A dermoscopic close-up of a skin lesion.
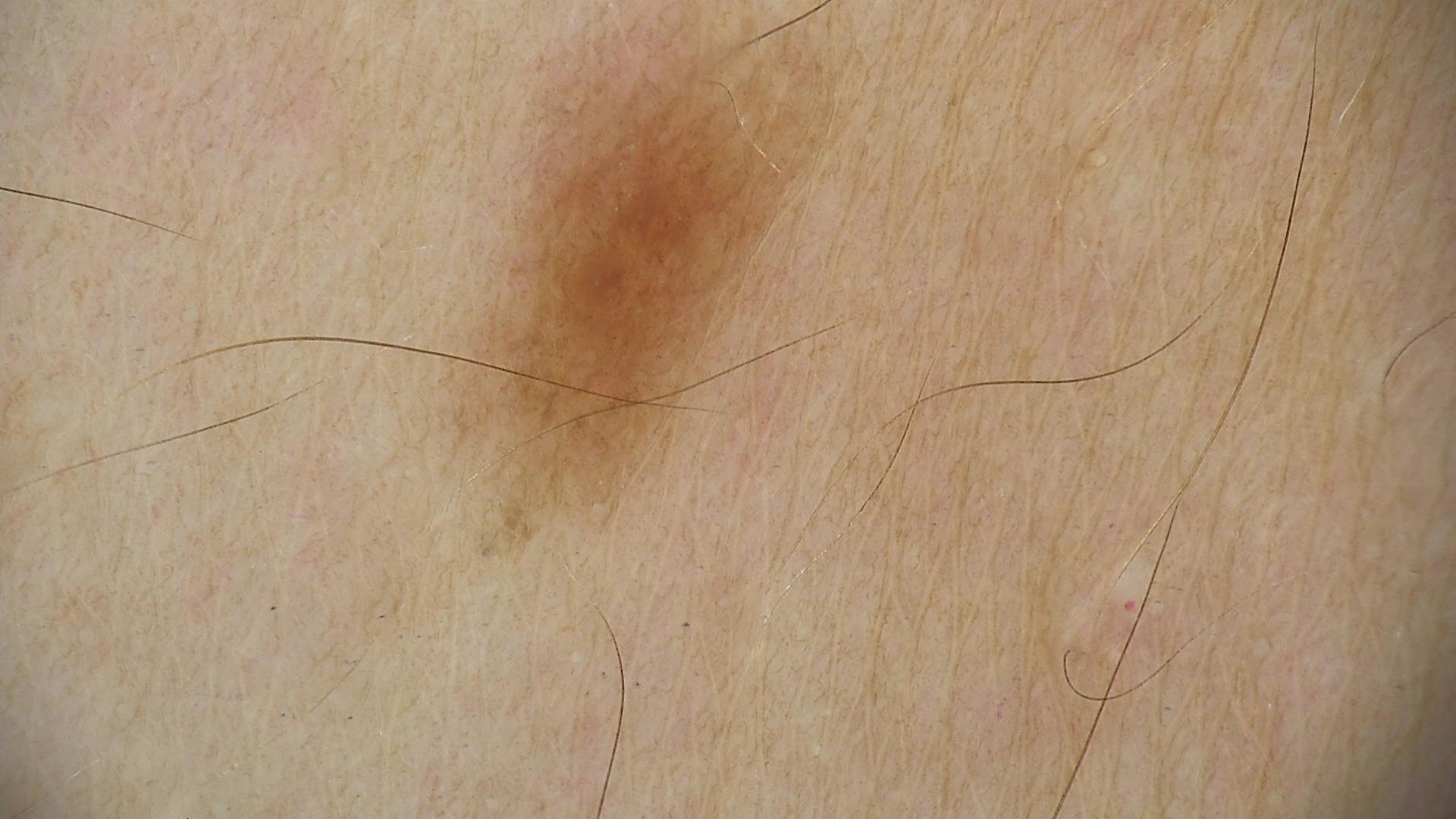Impression:
Classified as a banal lesion — a junctional nevus.